Skin type III · by history, prior skin cancer (patient or family), pesticide exposure, and prior malignancy (patient or family) · a smartphone photograph of a skin lesion · a male subject in their 40s: 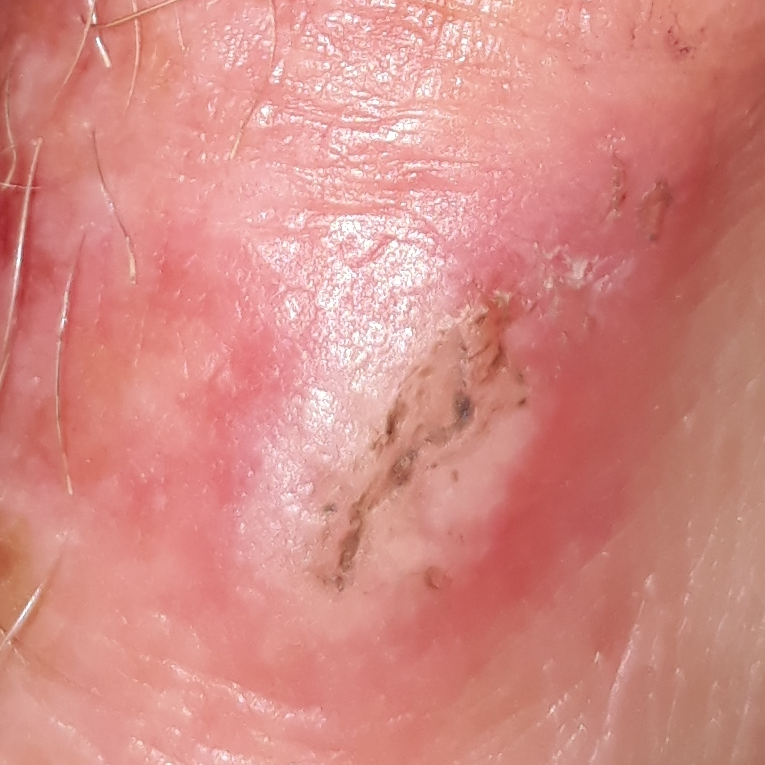The lesion measures approximately 13 × 10 mm. By the patient's account, the lesion itches, has grown, and is elevated. On biopsy, the diagnosis was an actinic keratosis.